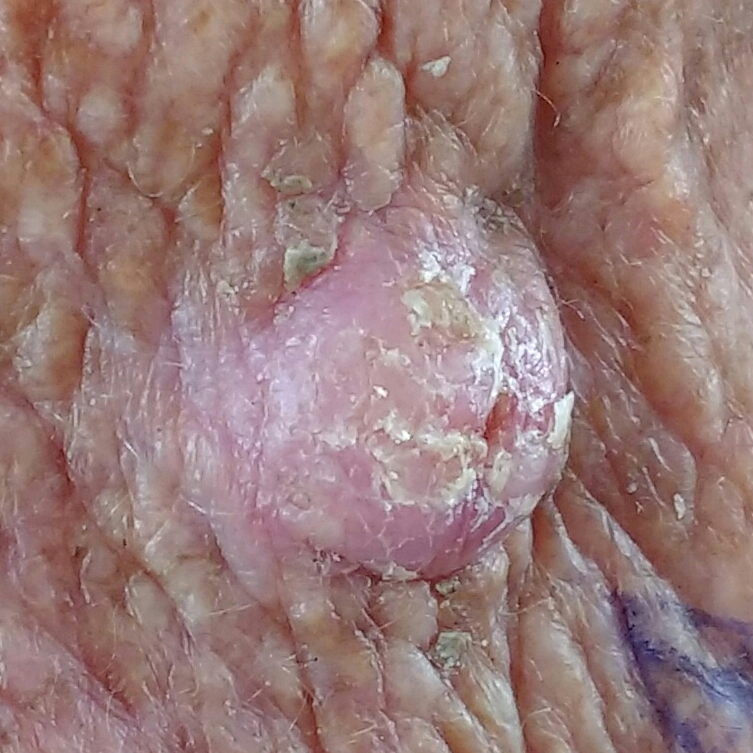Findings:
• patient: female, aged 79
• FST: II
• imaging: clinical photo
• body site: the chest
• lesion size: approx. 12 × 10 mm
• diagnosis: squamous cell carcinoma (biopsy-proven)